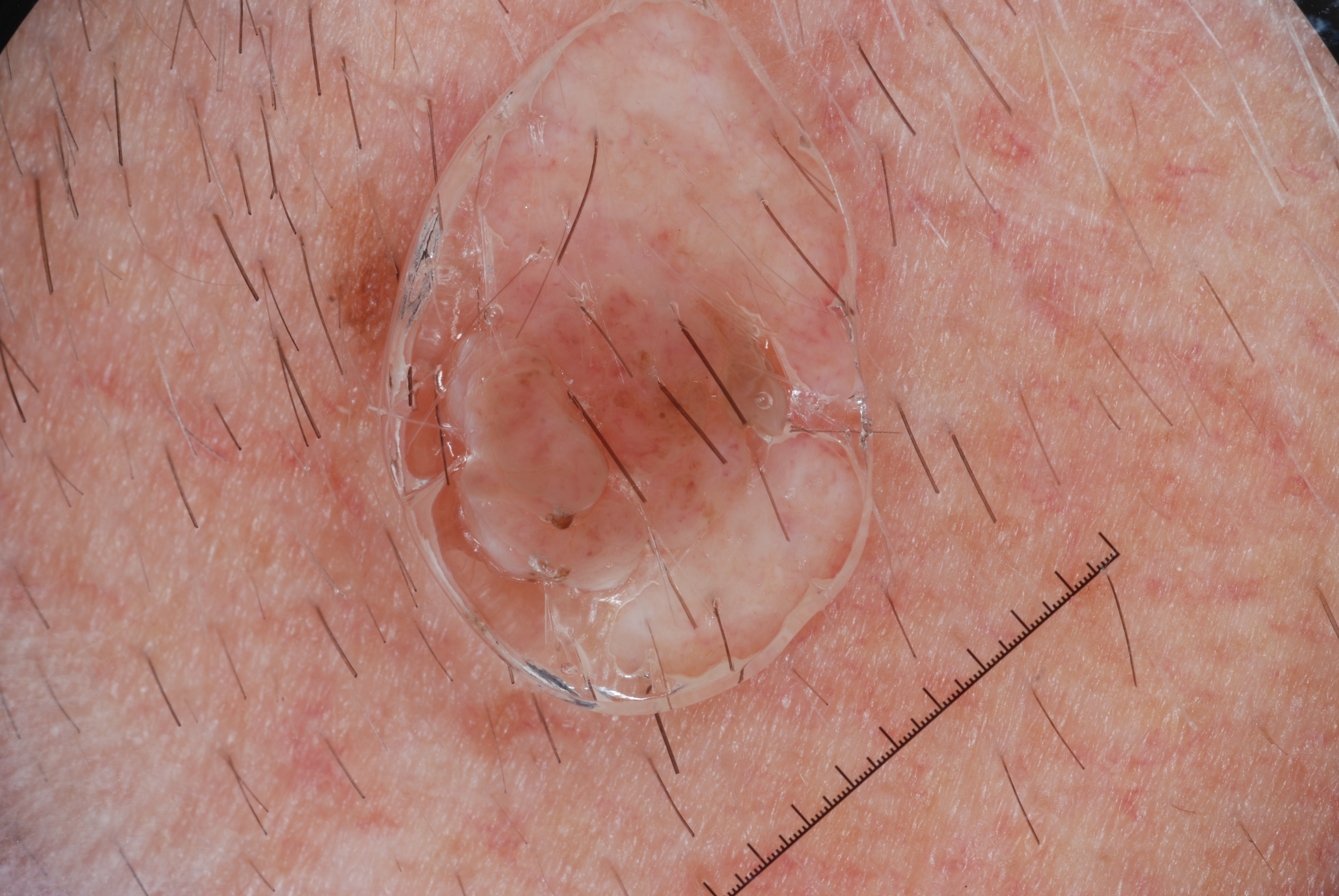Image and clinical context: This is a dermoscopic photograph of a skin lesion. The subject is a male in their mid-60s. With coordinates (x1, y1, x2, y2), lesion location: bbox=[379, 5, 881, 723]. Dermoscopic examination shows no streaks, milia-like cysts, pigment network, or negative network. Impression: Diagnosed as a melanocytic nevus.